A dermoscopic photograph of a skin lesion · a male patient aged 78-82.
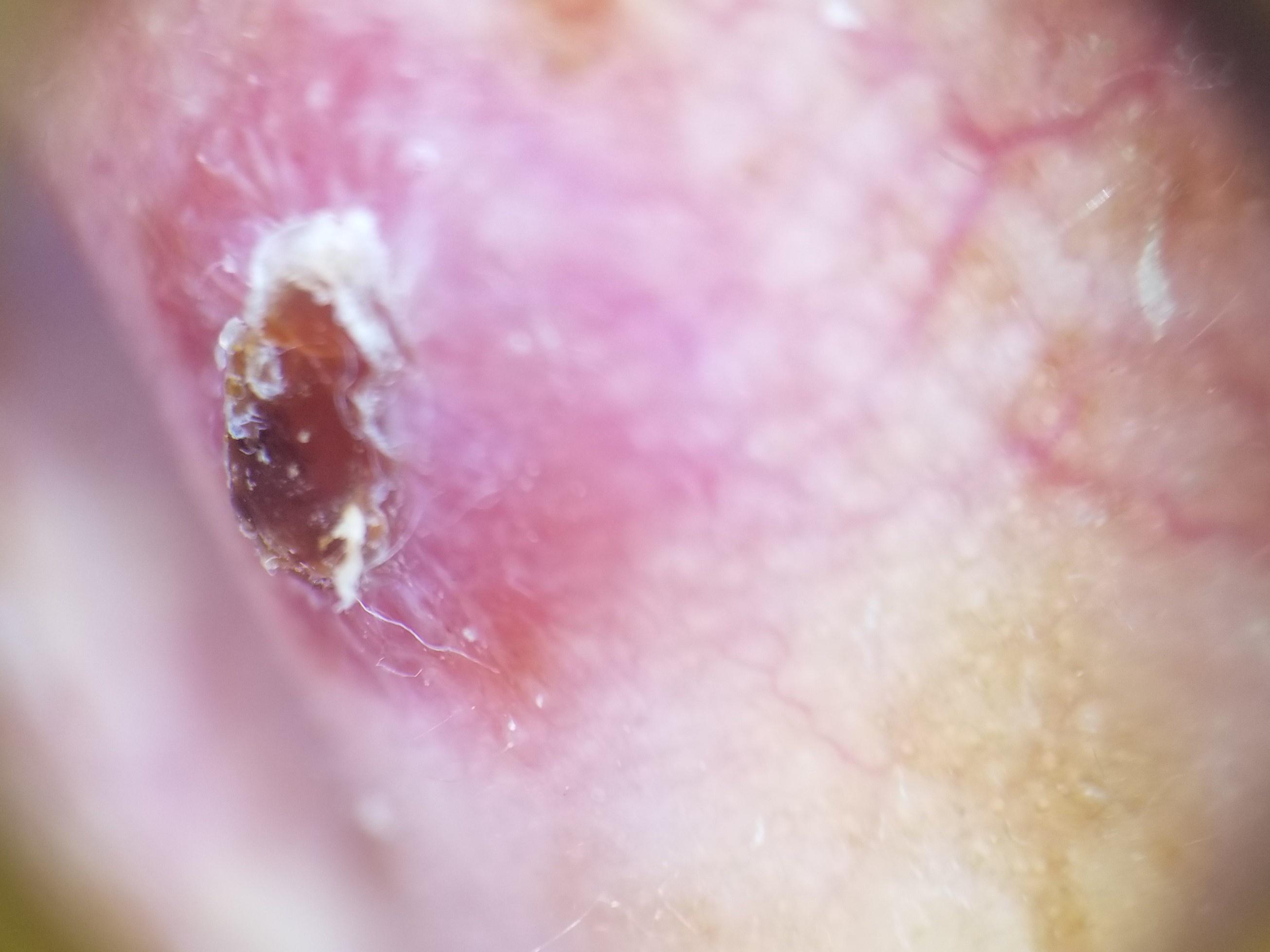diagnosis:
  name: Squamous cell carcinoma
  malignancy: malignant
  confirmation: histopathology
  lineage: epidermal